A male subject aged 28-32. The chart records a previous melanoma. A dermatoscopic image of a skin lesion — 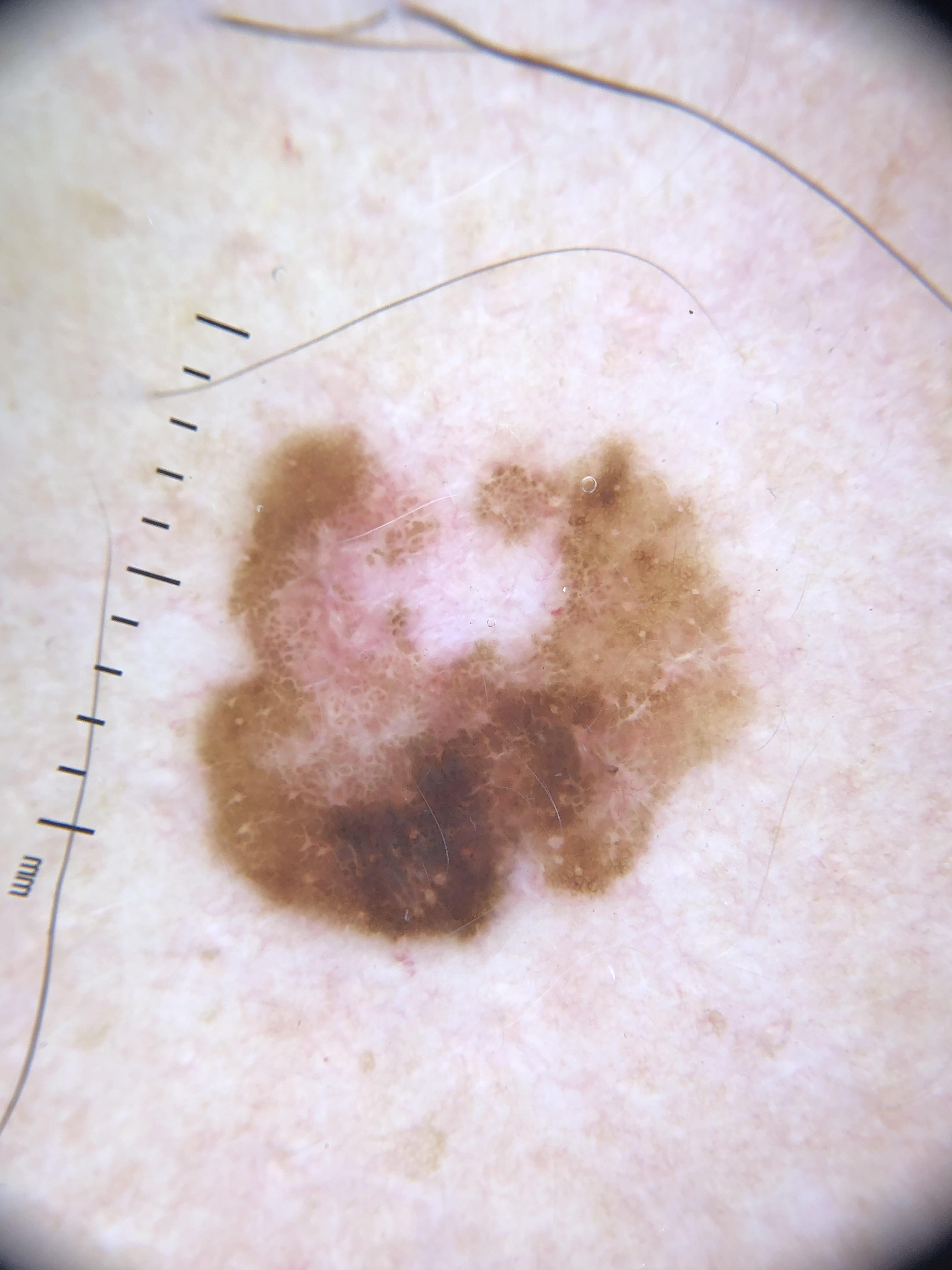The lesion involves the trunk. Histopathologically confirmed as a melanoma.